A clinical photograph of a skin lesion.
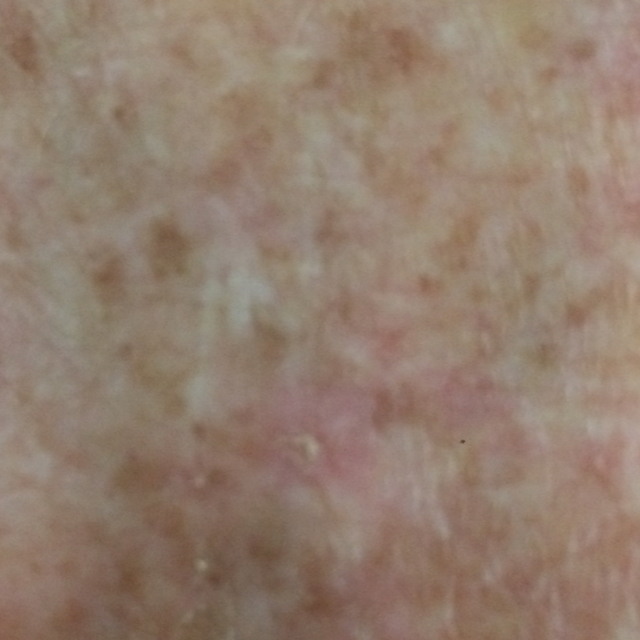symptoms: no growth
diagnosis: actinic keratosis (clinical consensus)